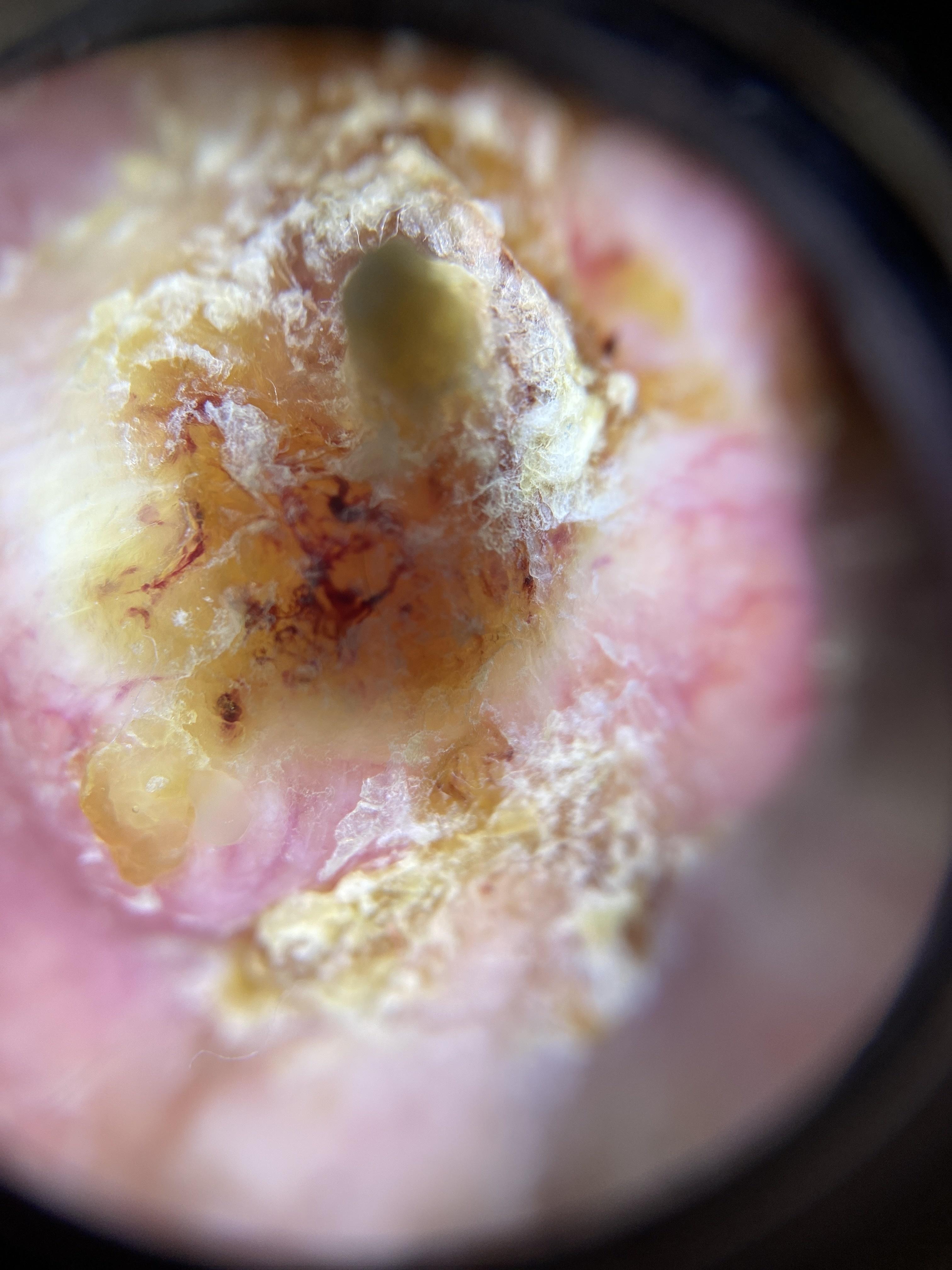Case summary: A contact-polarized dermoscopy image of a skin lesion. A female patient about 85 years old or older. Located on the head or neck. Conclusion: Histopathologically confirmed as a squamous cell carcinoma.